The subject is a female aged 18–29 · the photo was captured at a distance · located on the arm:
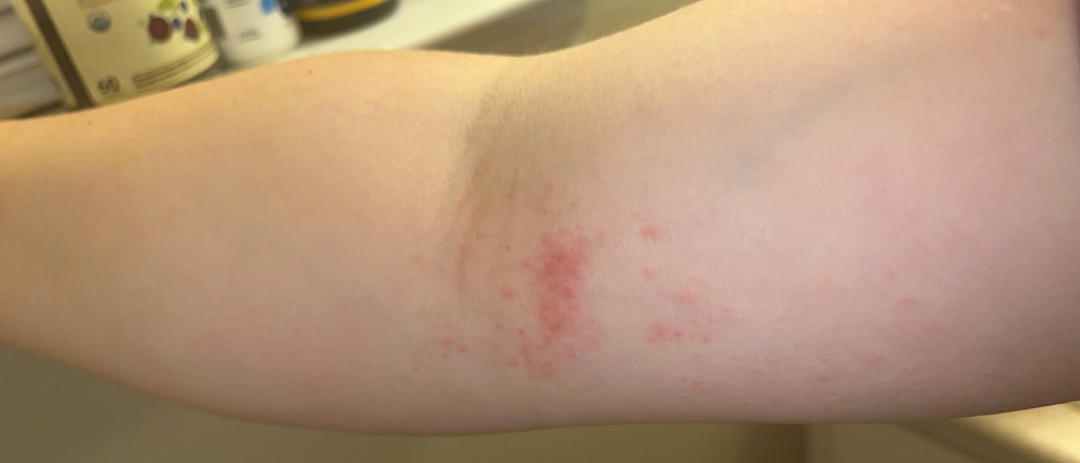{"differential": "Eczema"}